The arm is involved. The contributor reports the condition has been present for less than one week. The photo was captured at an angle. Texture is reported as raised or bumpy and fluid-filled. Reported lesion symptoms include itching and burning: 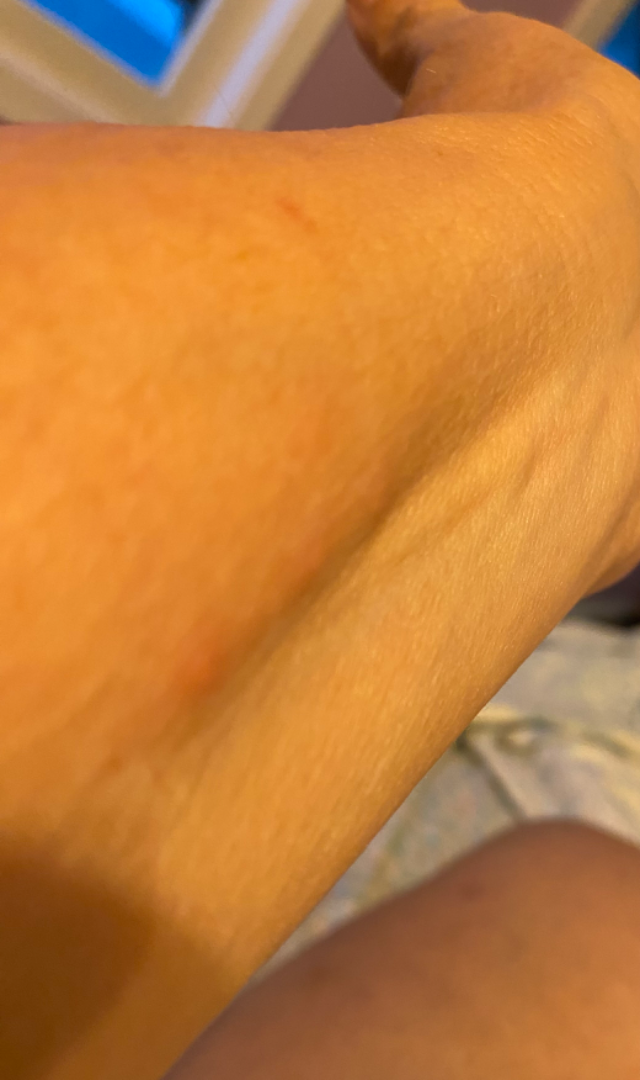| key | value |
|---|---|
| differential diagnosis | favoring Insect Bite; also raised was Urticaria; with consideration of Allergic Contact Dermatitis |